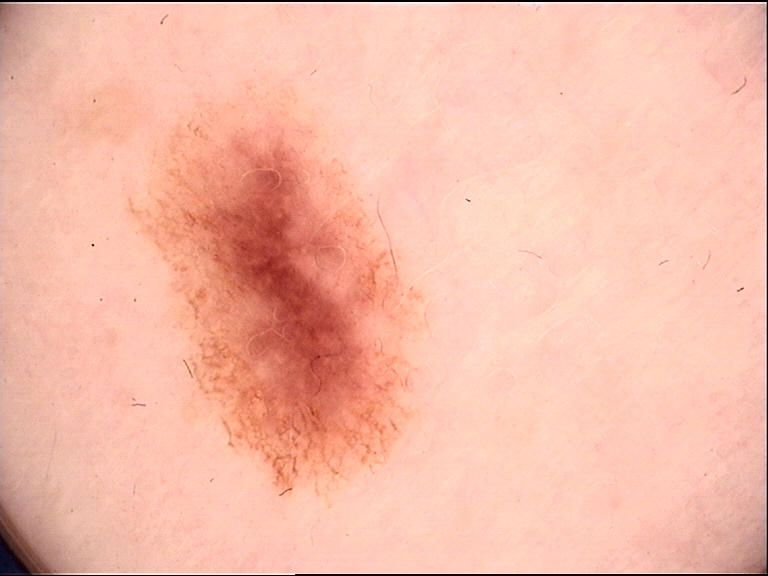{"diagnosis": {"name": "dysplastic junctional nevus", "code": "jd", "malignancy": "benign", "super_class": "melanocytic", "confirmation": "expert consensus"}}